The photo was captured at a distance · the subject is female · the lesion involves the leg and arm · symptoms reported: itching · self-categorized by the patient as a rash · the condition has been present for less than one week · texture is reported as raised or bumpy:
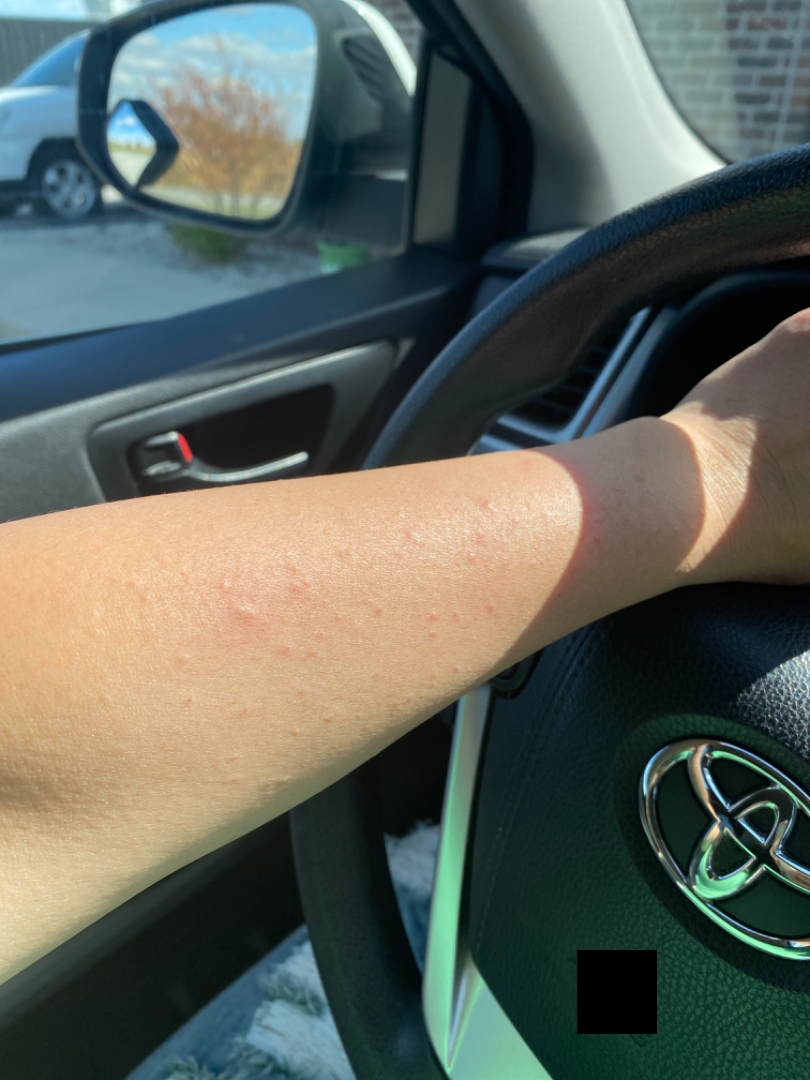The differential is split between Eczema, Viral dermatological disorders and Hypersensitivity.